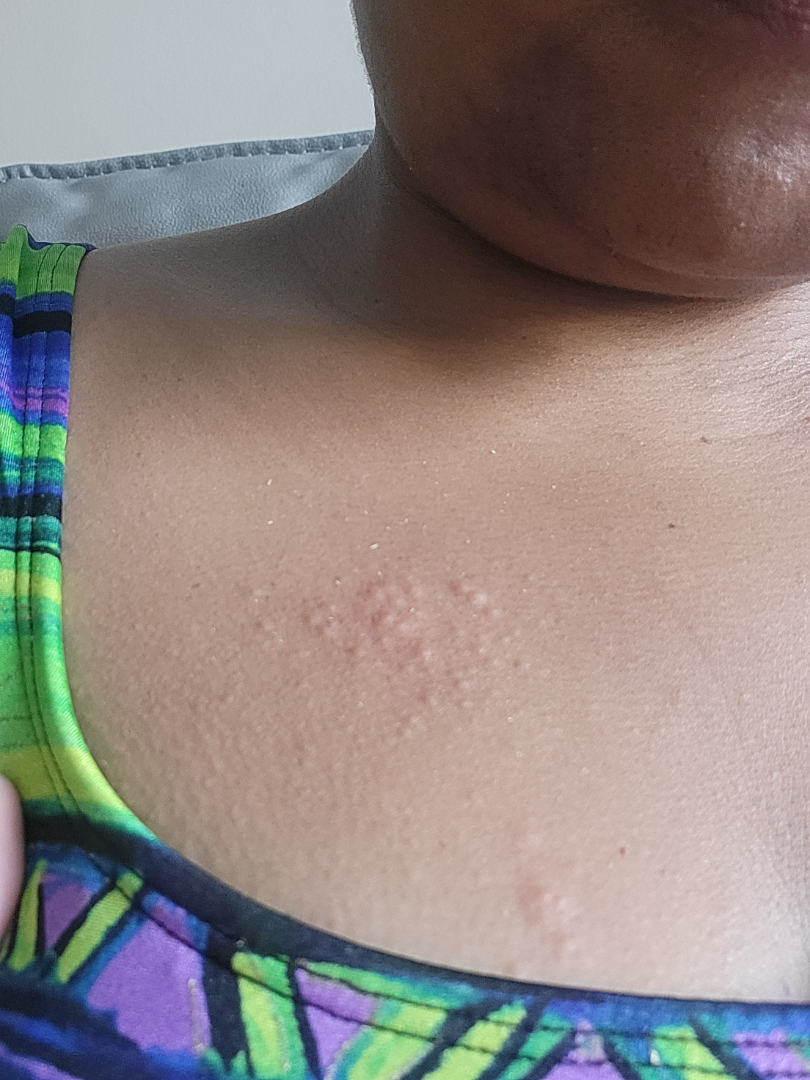Q: Who is the patient?
A: female, age 30–39
Q: What is the framing?
A: close-up
Q: What is the dermatologist's impression?
A: Insect Bite (possible); Herpes Zoster (possible); Allergic Contact Dermatitis (possible)